The affected area is the arm · this is a close-up image:
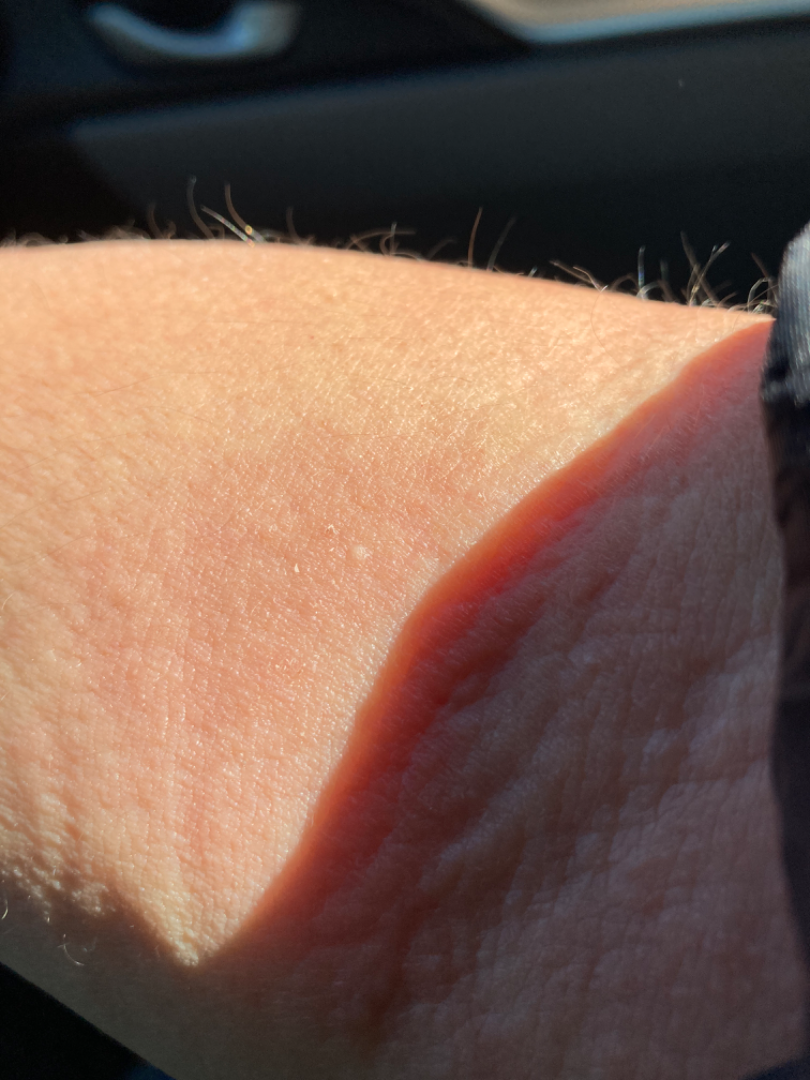assessment: not assessable